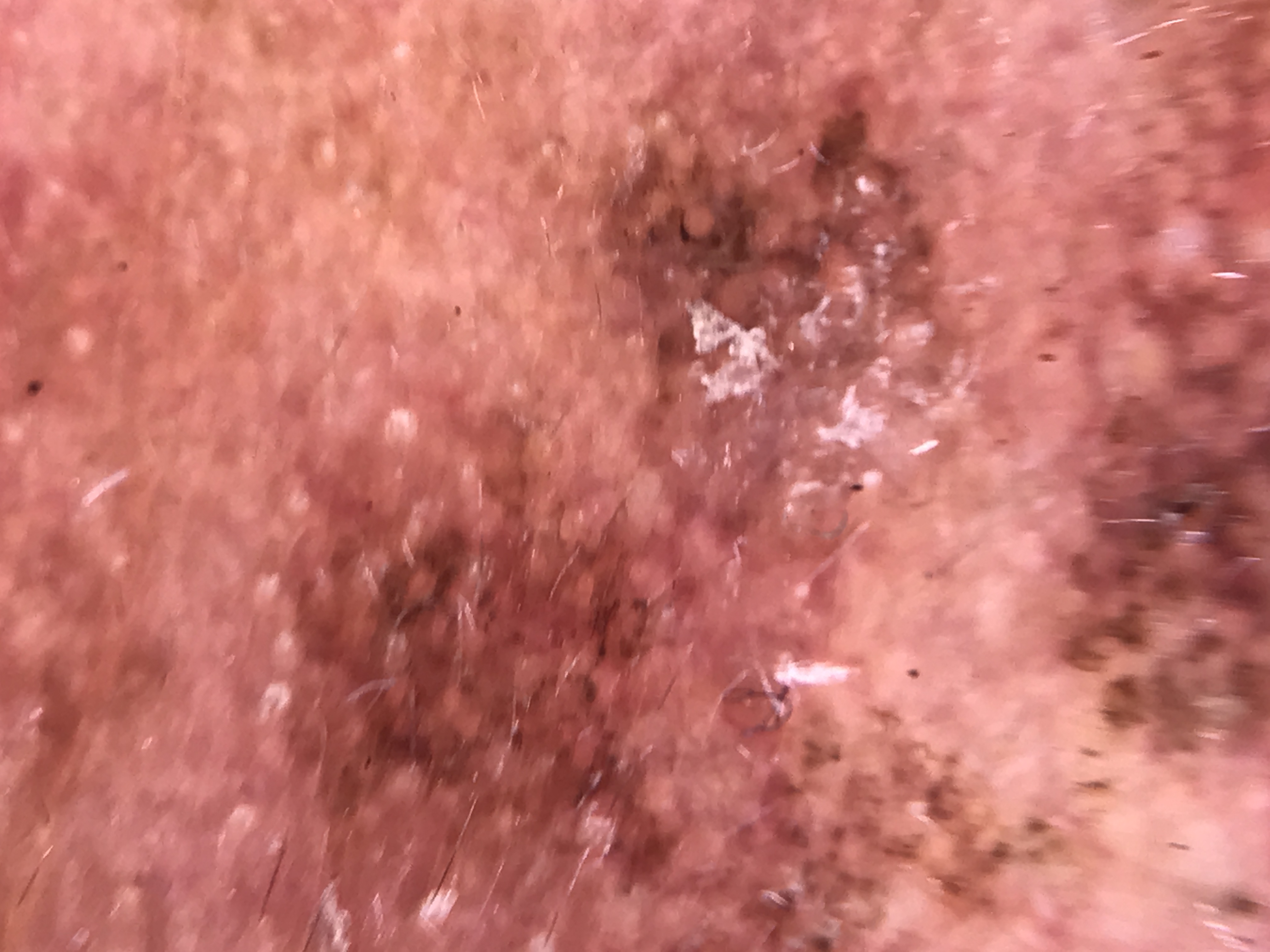A dermoscopic image of a skin lesion.
This is a keratinocytic lesion.
Classified as an actinic keratosis.